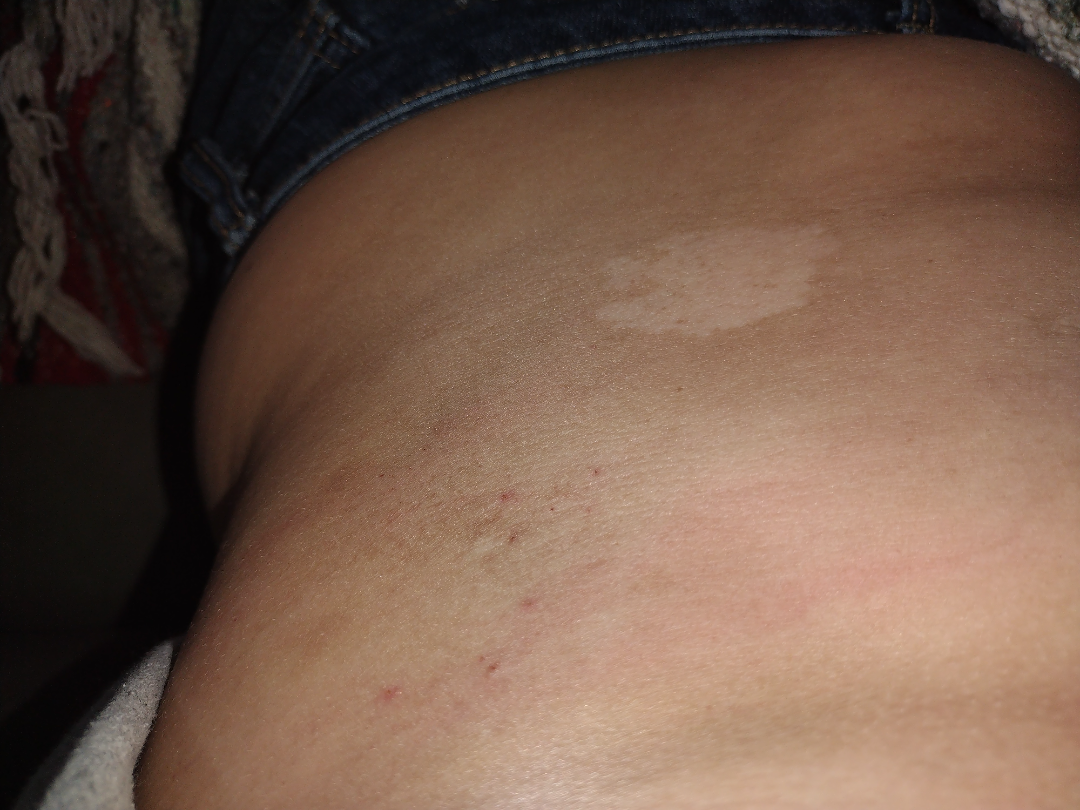Review: On remote review of the image: Pityriasis alba and Melanocytic Nevus were each considered, in no particular order; less likely is Nevus anemicus.